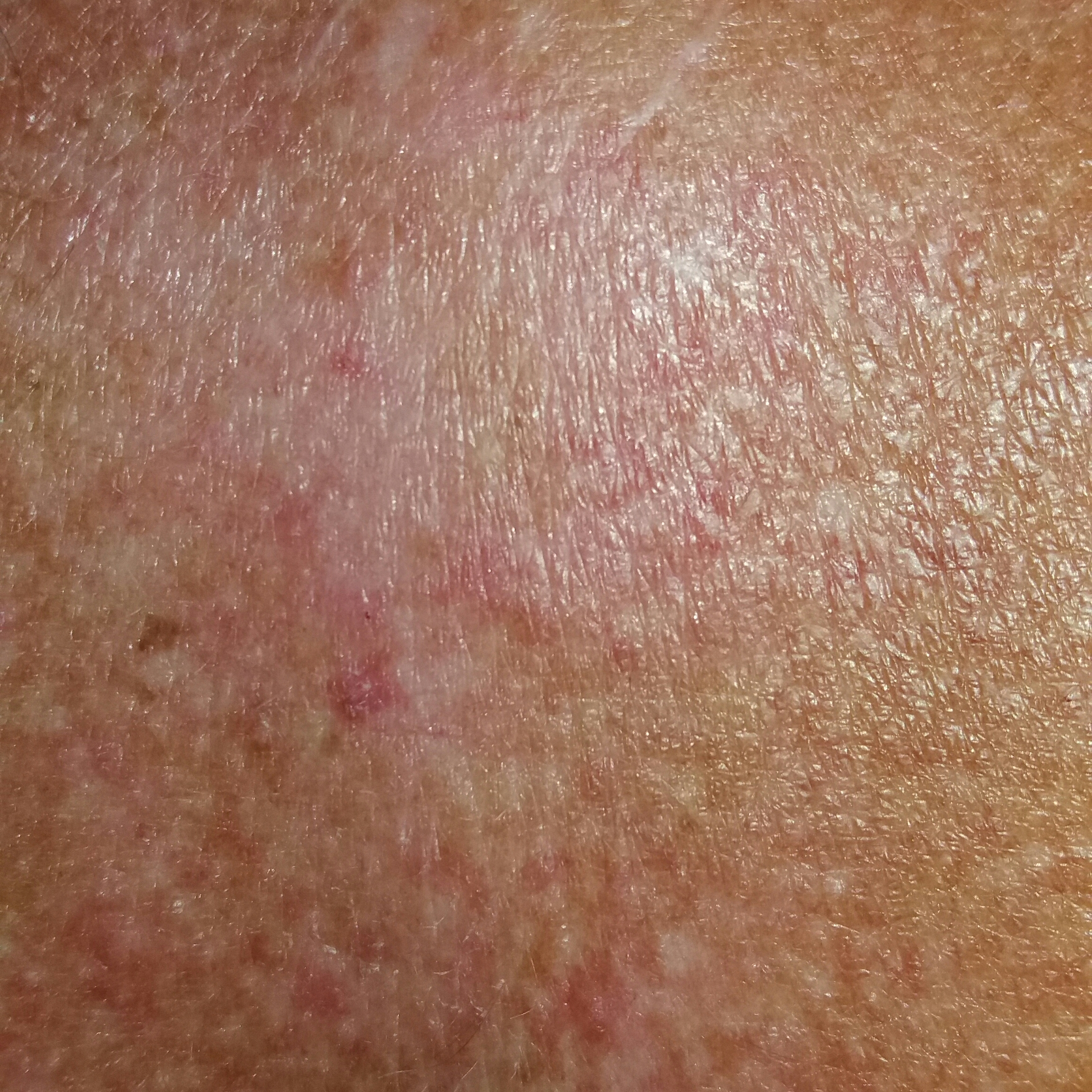  image: smartphone clinical photo
  patient:
    age: 51
  lesion_location: the back
  symptoms:
    present:
      - itching
  diagnosis:
    name: actinic keratosis
    code: ACK
    malignancy: indeterminate
    confirmation: clinical consensus